A dermatoscopic image of a skin lesion: 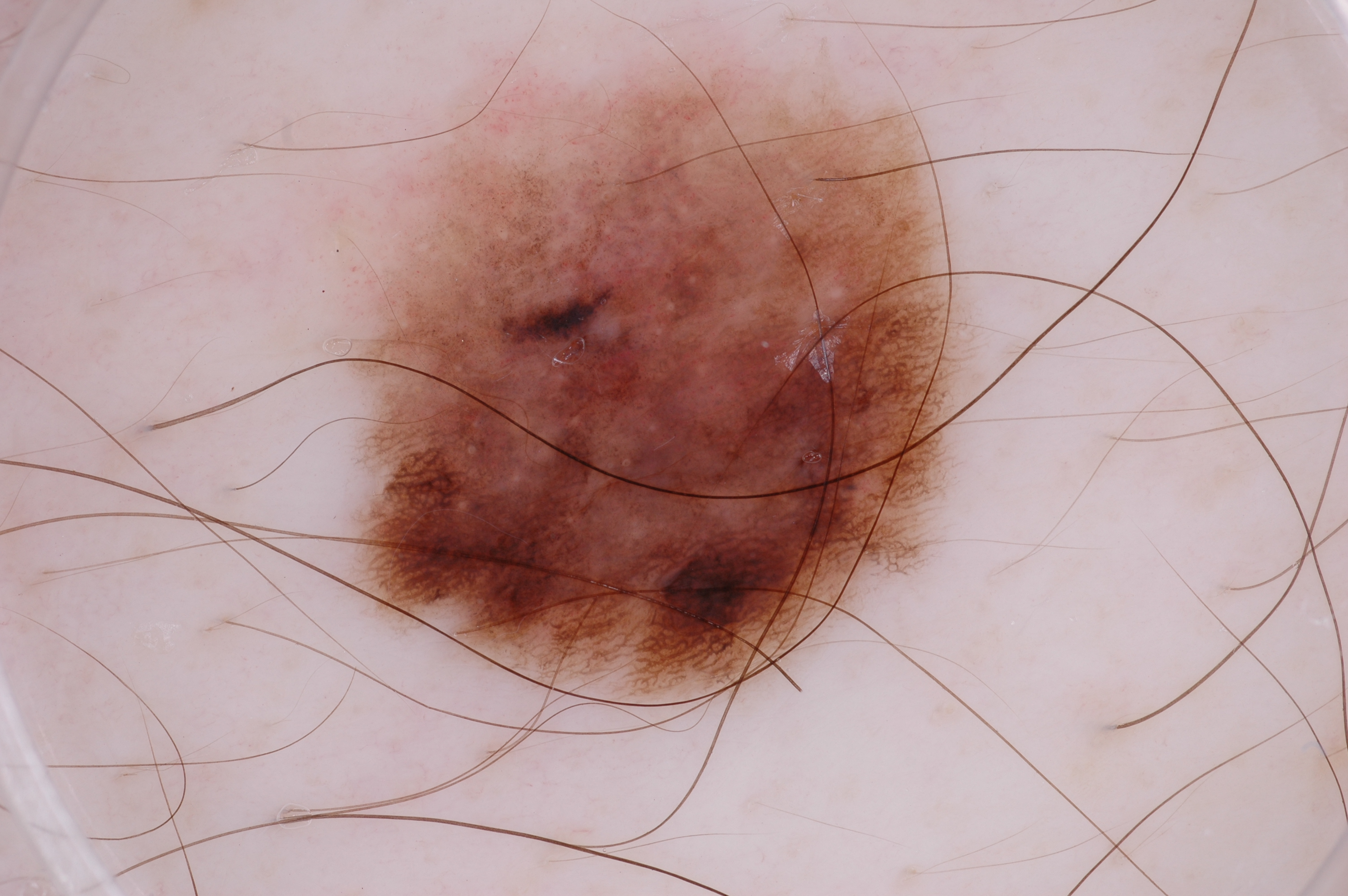lesion bbox: left=335, top=45, right=981, bottom=706
dermoscopic findings: pigment network
assessment: a melanoma, a malignant skin lesion